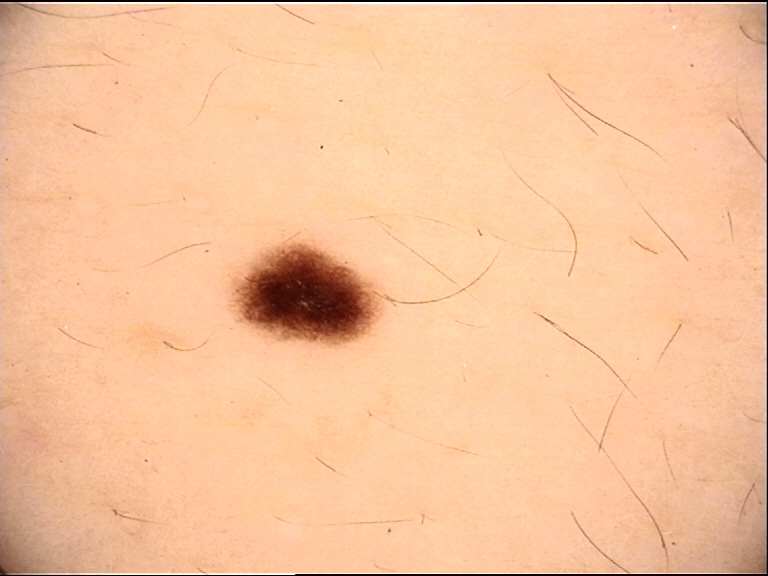The diagnostic label was a junctional nevus.